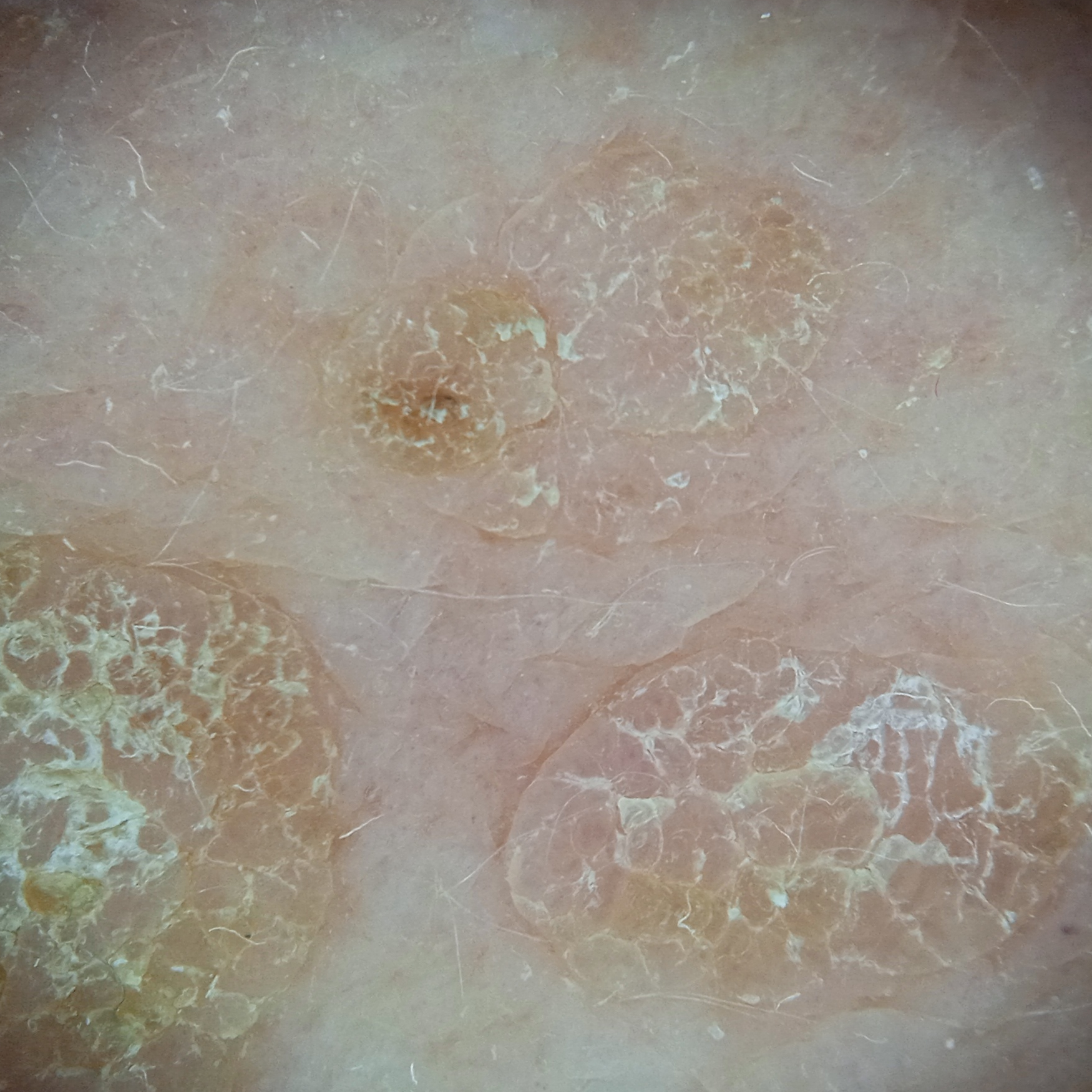image: dermoscopy
sun reaction: skin reddens painfully with sun exposure
relevant history: immunosuppression, a prior organ transplant
patient: female, 55 years of age
nevus count: a moderate number of melanocytic nevi
clinical context: research study (no referral diagnosis)
anatomic site: the back
lesion size: 10.6 mm
diagnostic label: seborrheic keratosis (dermatologist consensus)